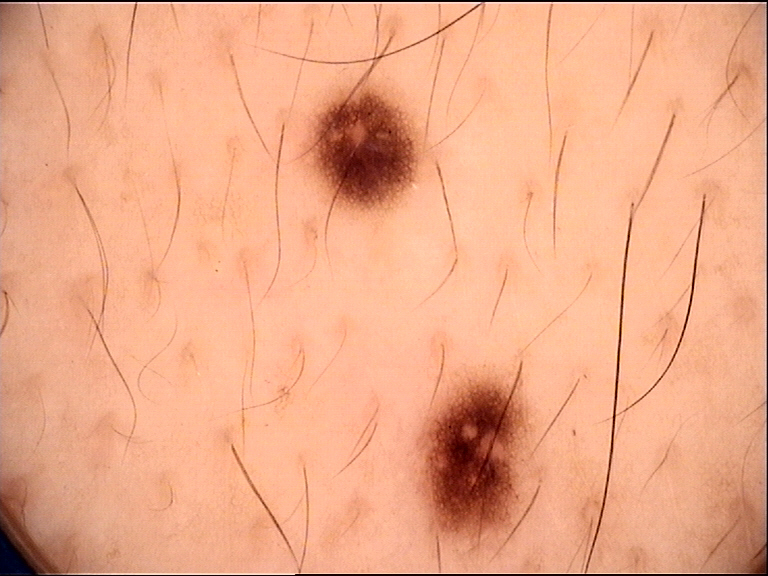A dermoscopy image of a single skin lesion. Labeled as a dysplastic junctional nevus.